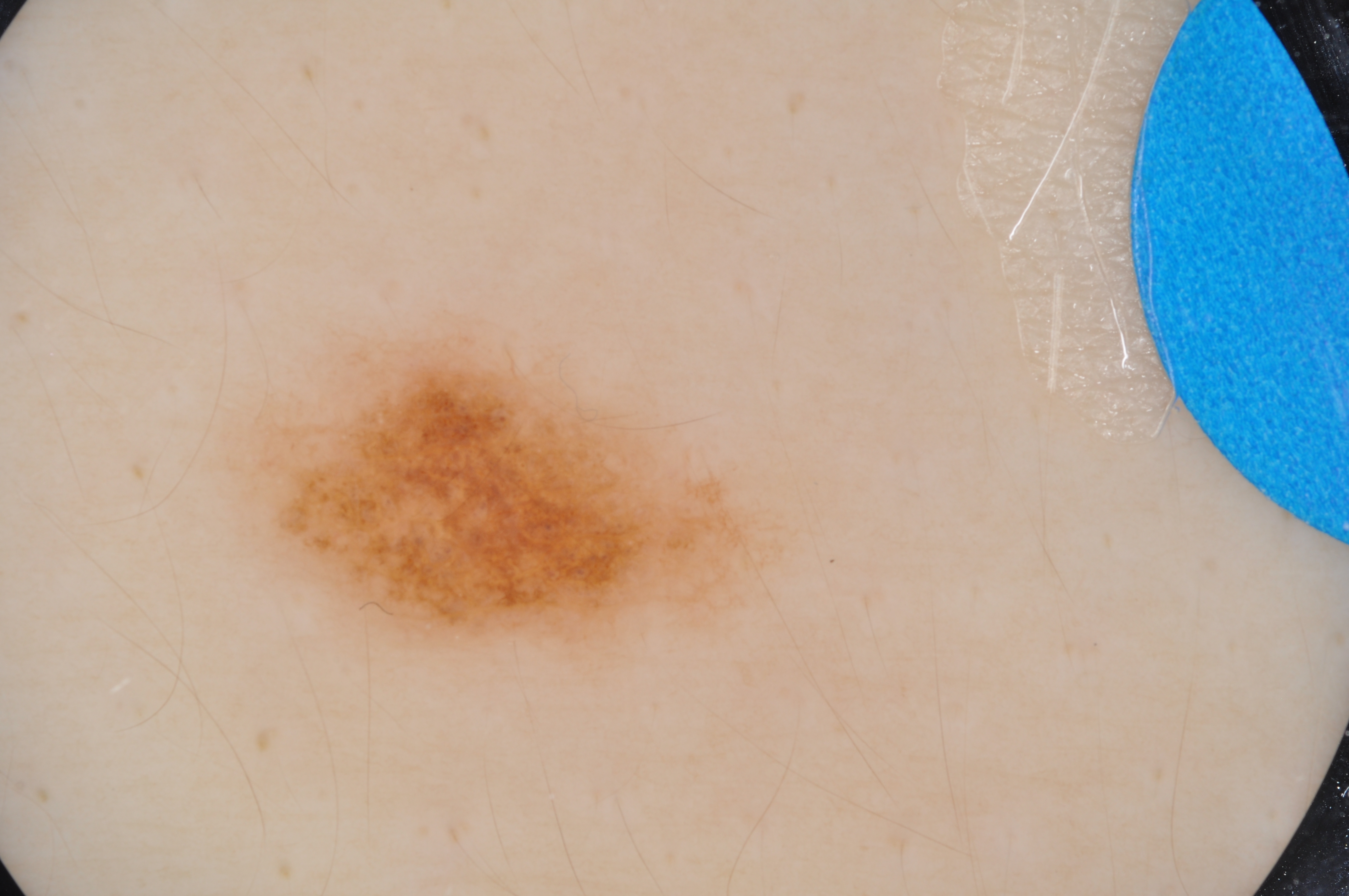The patient is a female aged approximately 15.
Dermoscopy of a skin lesion.
Dermoscopic review identifies no pigment network, negative network, milia-like cysts, streaks, or globules.
As (left, top, right, bottom), the visible lesion spans bbox=[226, 327, 786, 672].
A mid-sized lesion within the field.
The lesion was assessed as a melanocytic nevus.